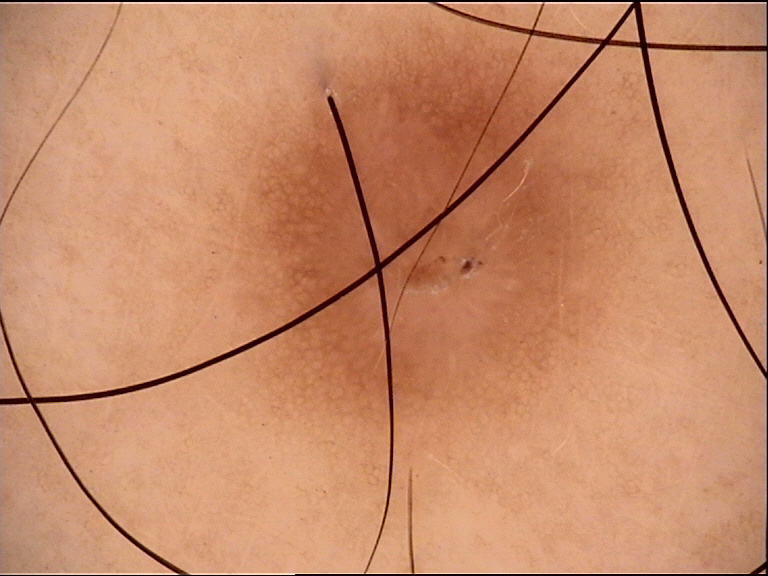imaging — dermoscopy
class — dermatofibroma (expert consensus)